A skin lesion imaged with a dermatoscope: 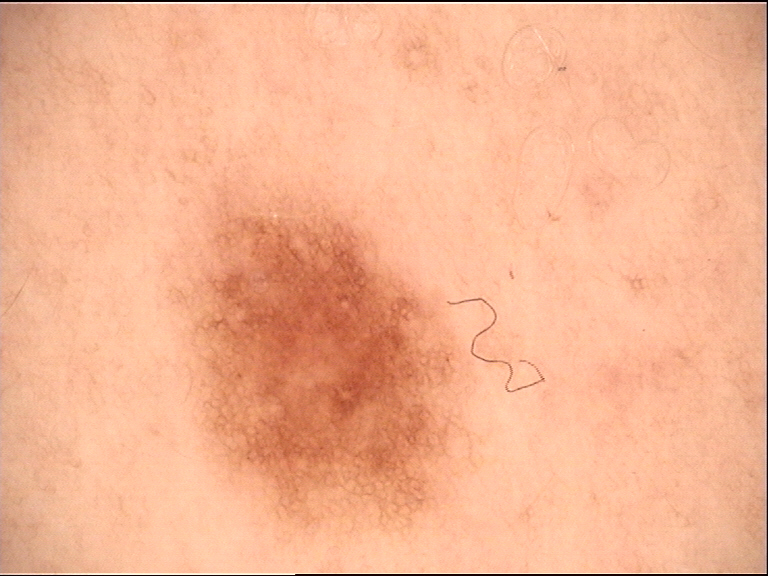Findings:
- label — dysplastic junctional nevus (expert consensus)